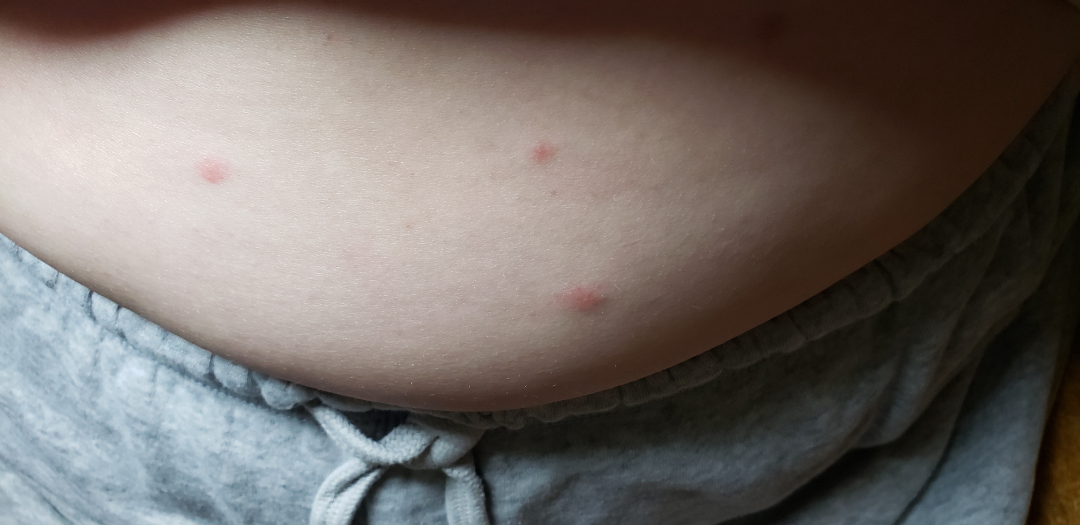The case was indeterminate on photographic review.